A dermoscopic close-up of a skin lesion.
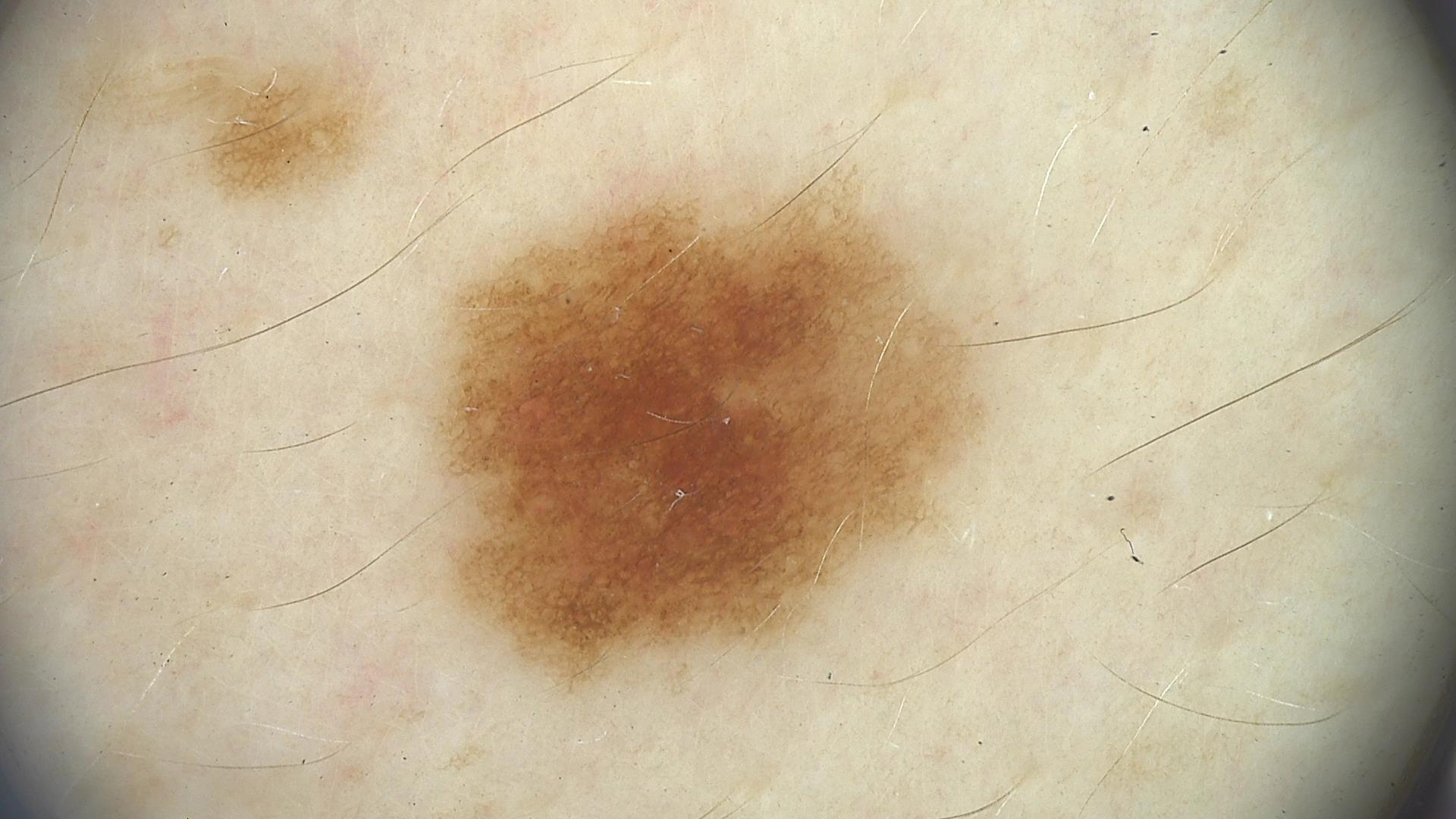Case:
• diagnostic label: dysplastic junctional nevus (expert consensus)